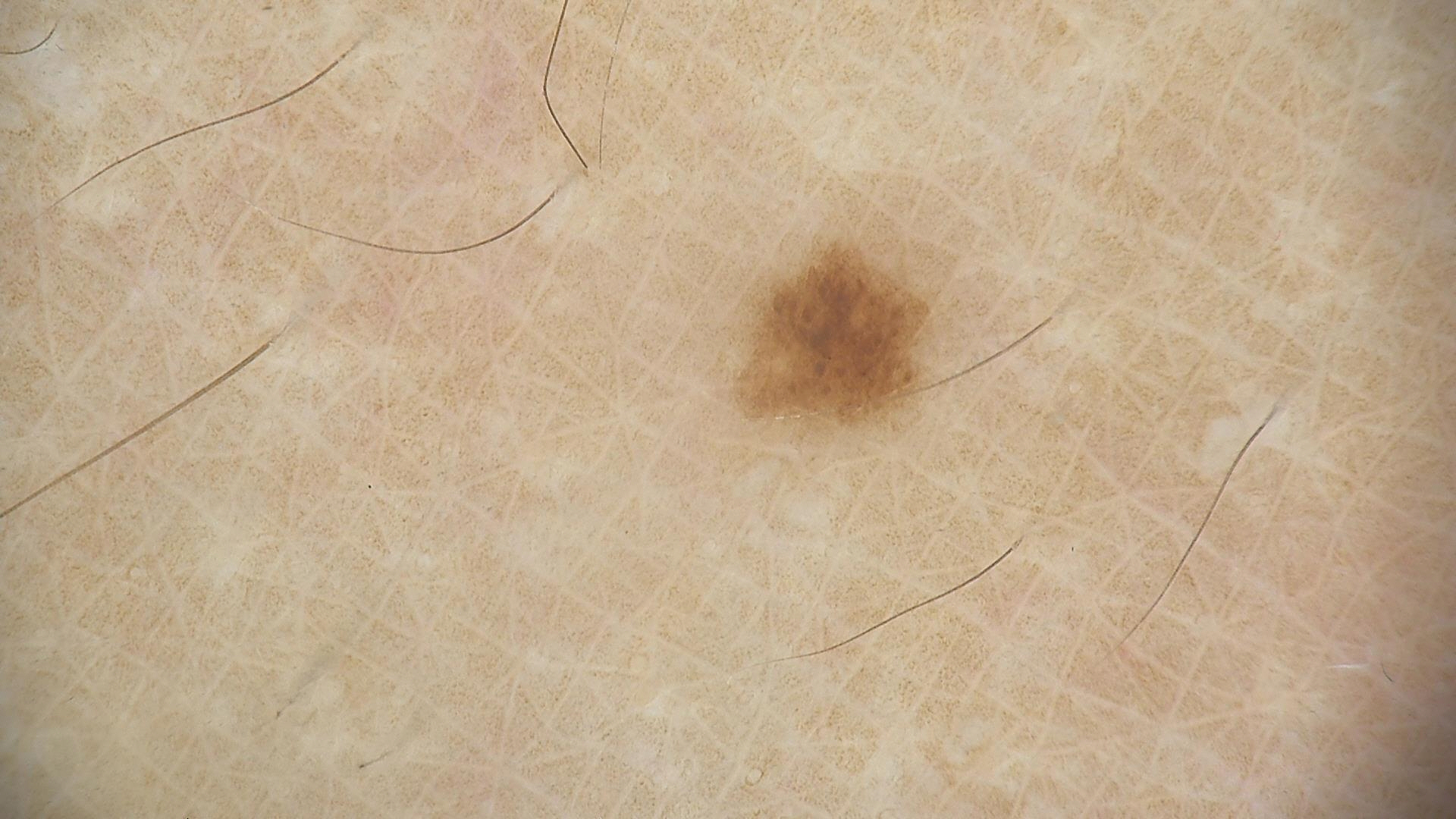modality = dermoscopy
label = dysplastic junctional nevus (expert consensus)